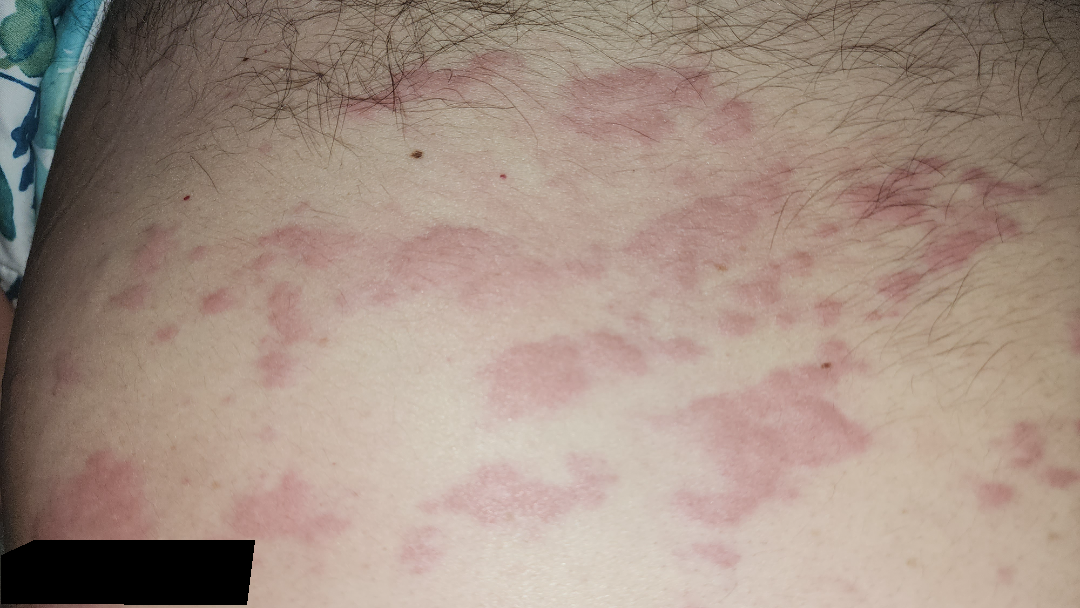Single-reviewer assessment: most likely Urticaria; possibly Allergic Contact Dermatitis.